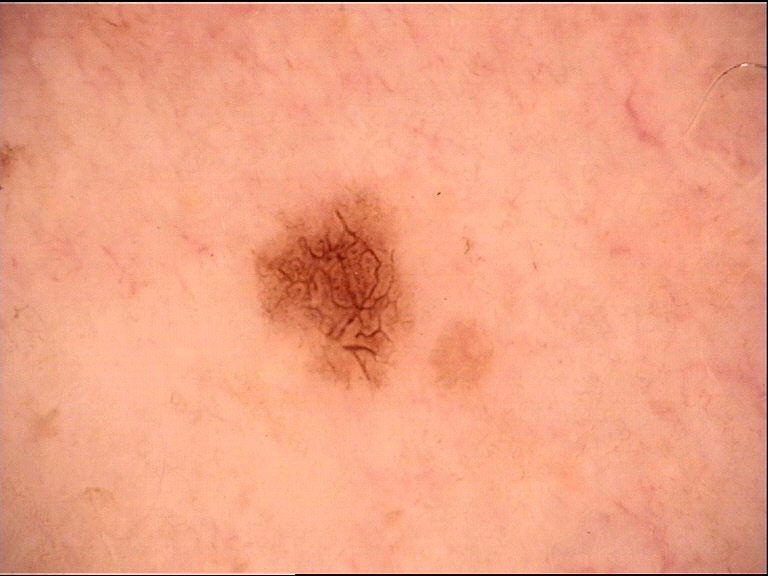label = dysplastic junctional nevus (expert consensus).